A female patient aged 83 or over, a dermatoscopic image of a skin lesion:
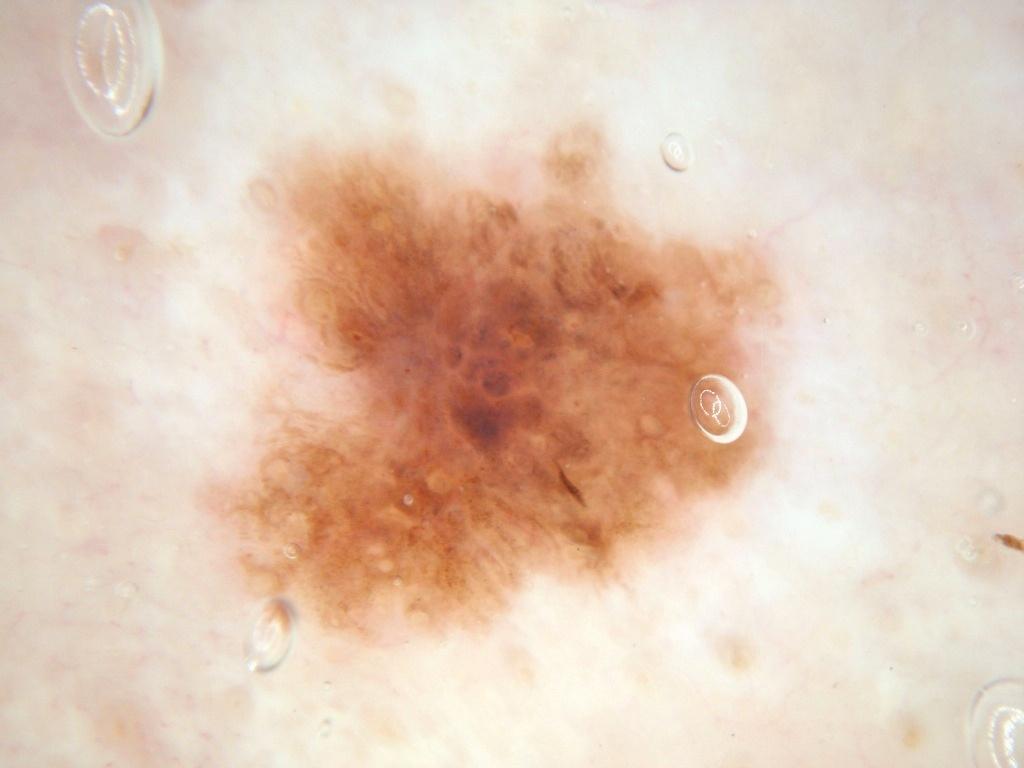| field | value |
|---|---|
| dermoscopic findings | negative network, pigment network, and globules; absent: milia-like cysts and streaks |
| lesion location | 179 117 785 662 |
| diagnosis | a melanoma |